The lesion is described as raised or bumpy · the arm is involved · the patient reports the condition has been present for less than one week · the photograph is a close-up of the affected area · the lesion is associated with itching · the patient is 18–29, male.
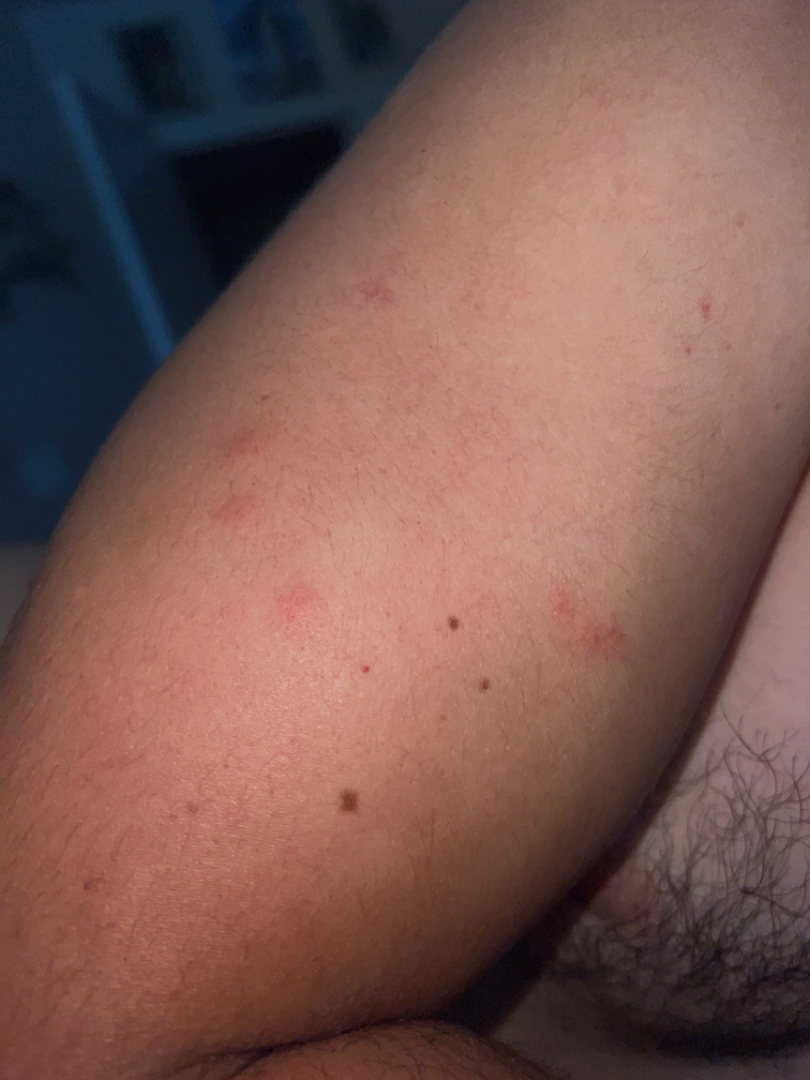Review:
On independent review by the dermatologists: the favored diagnosis is Insect Bite.